The affected area is the head or neck. The patient is 18–29, male. An image taken at a distance: 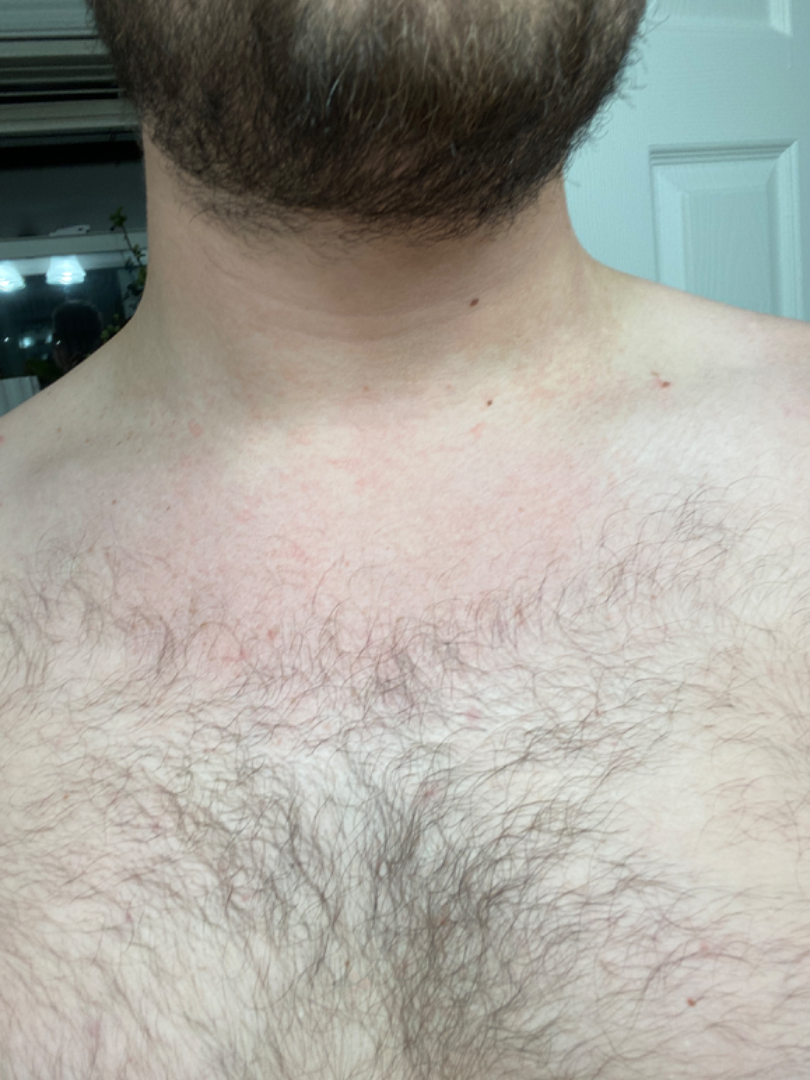{
  "assessment": "unable to determine"
}